The patient describes having few moles overall; on a questionnaire the patient reported a history of sunbed use, a family history of skin cancer, no personal history of cancer, and no prior organ transplant; the patient says their skin reddens painfully with sun exposure; a clinical photograph of a skin lesion; a female subject 48 years of age; imaged for a research study, with no referral diagnosis recorded:
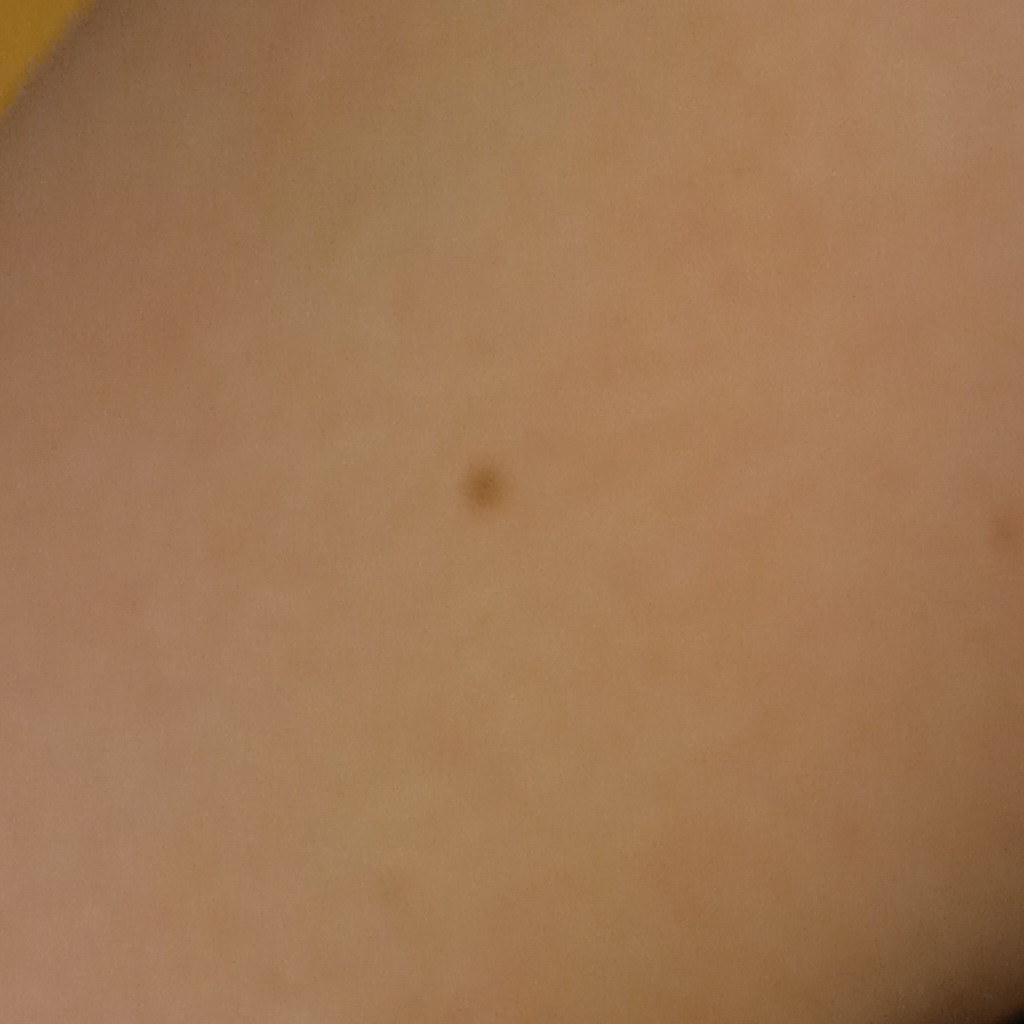The lesion is located on an arm. Measuring roughly 1.8 mm. The lesion was assessed as a melanocytic nevus.